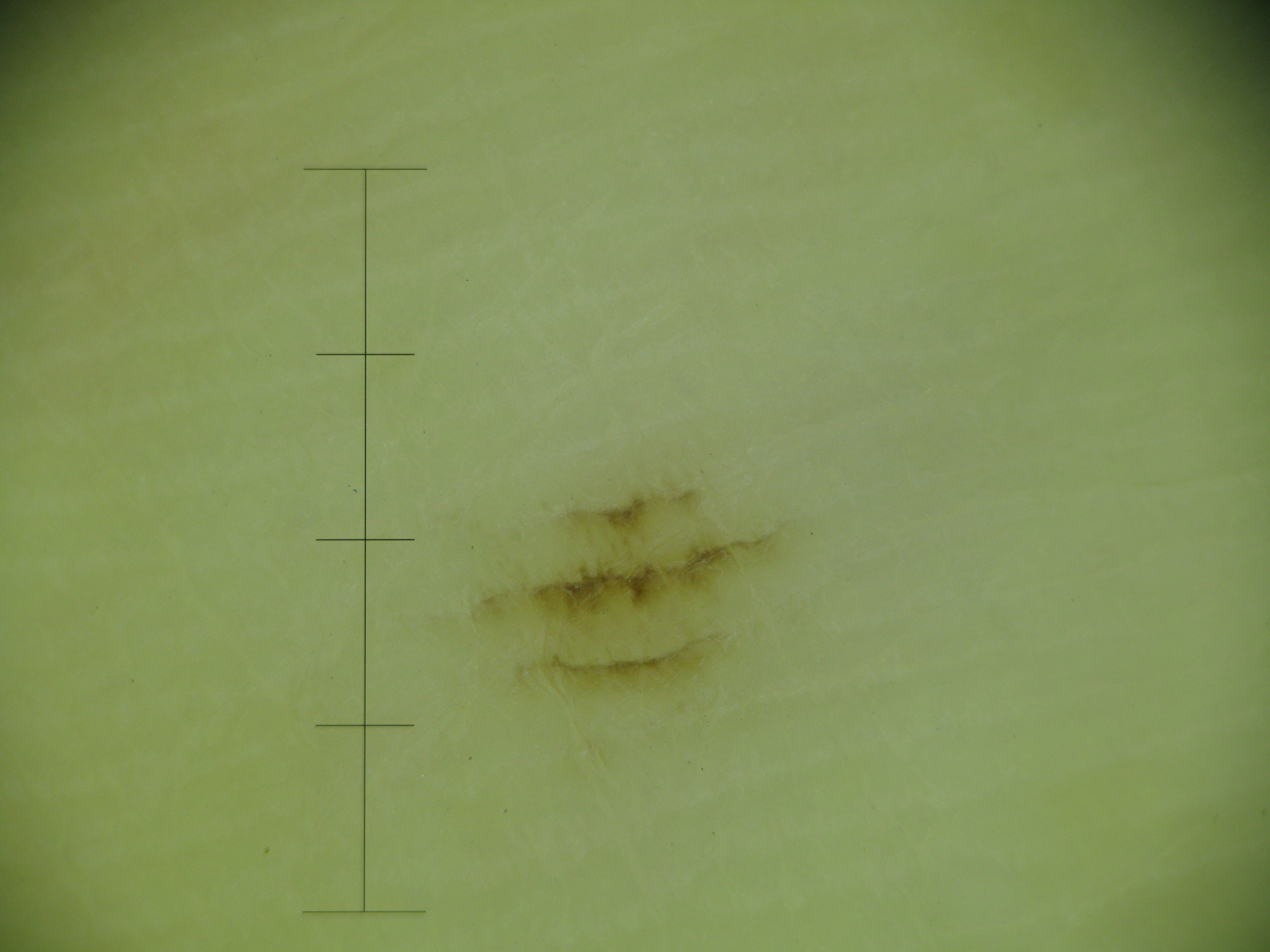modality: dermatoscopy
diagnostic label: acral junctional nevus (expert consensus)